A dermoscopic view of a skin lesion:
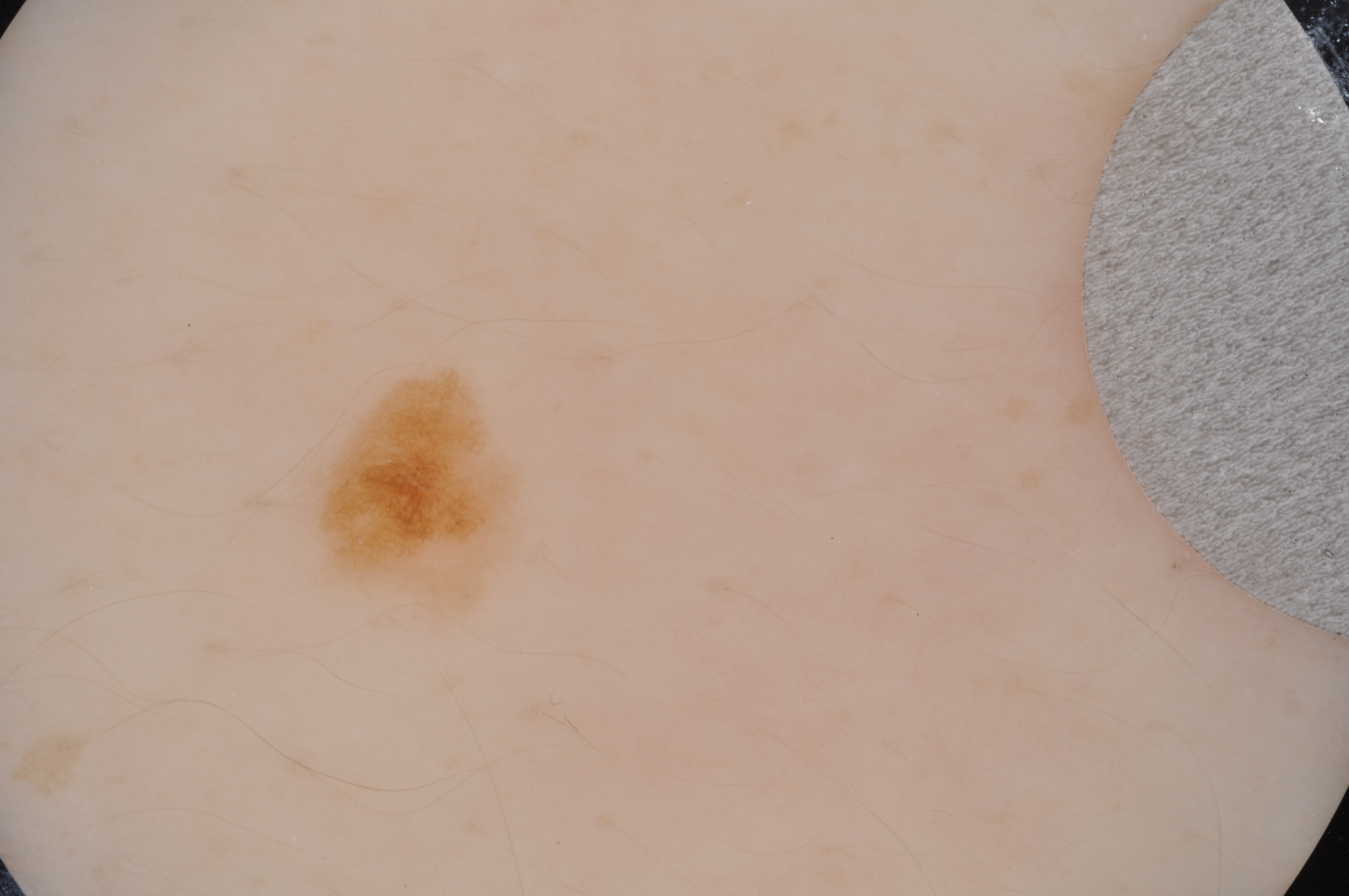absent dermoscopic findings=streaks and globules; location=<bbox>310, 366, 524, 621</bbox>; extent=small; impression=a benign lesion.